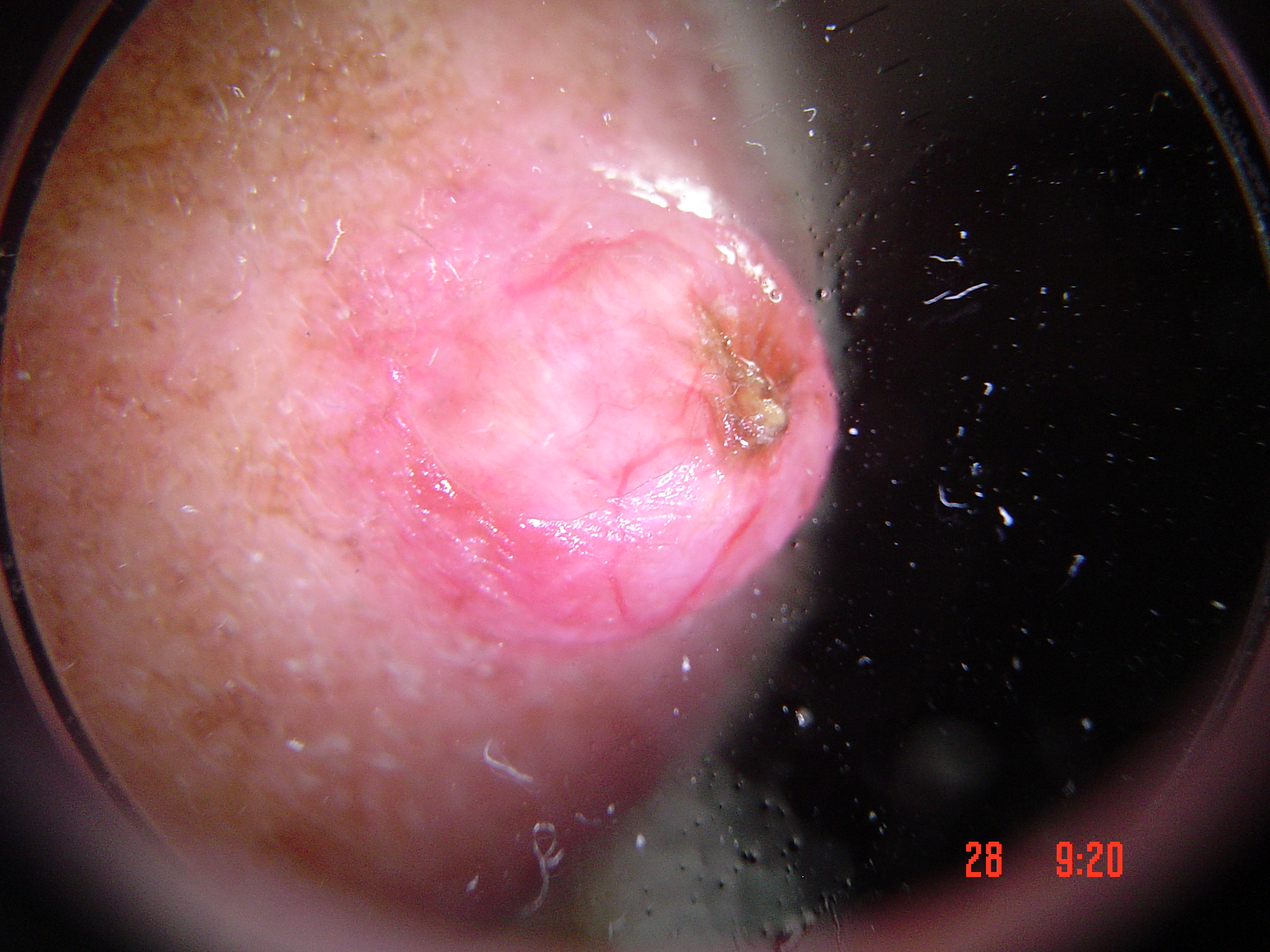Q: What is the imaging modality?
A: dermatoscopy
Q: What kind of lesion is this?
A: keratinocytic
Q: What did the workup show?
A: basal cell carcinoma (biopsy-proven)